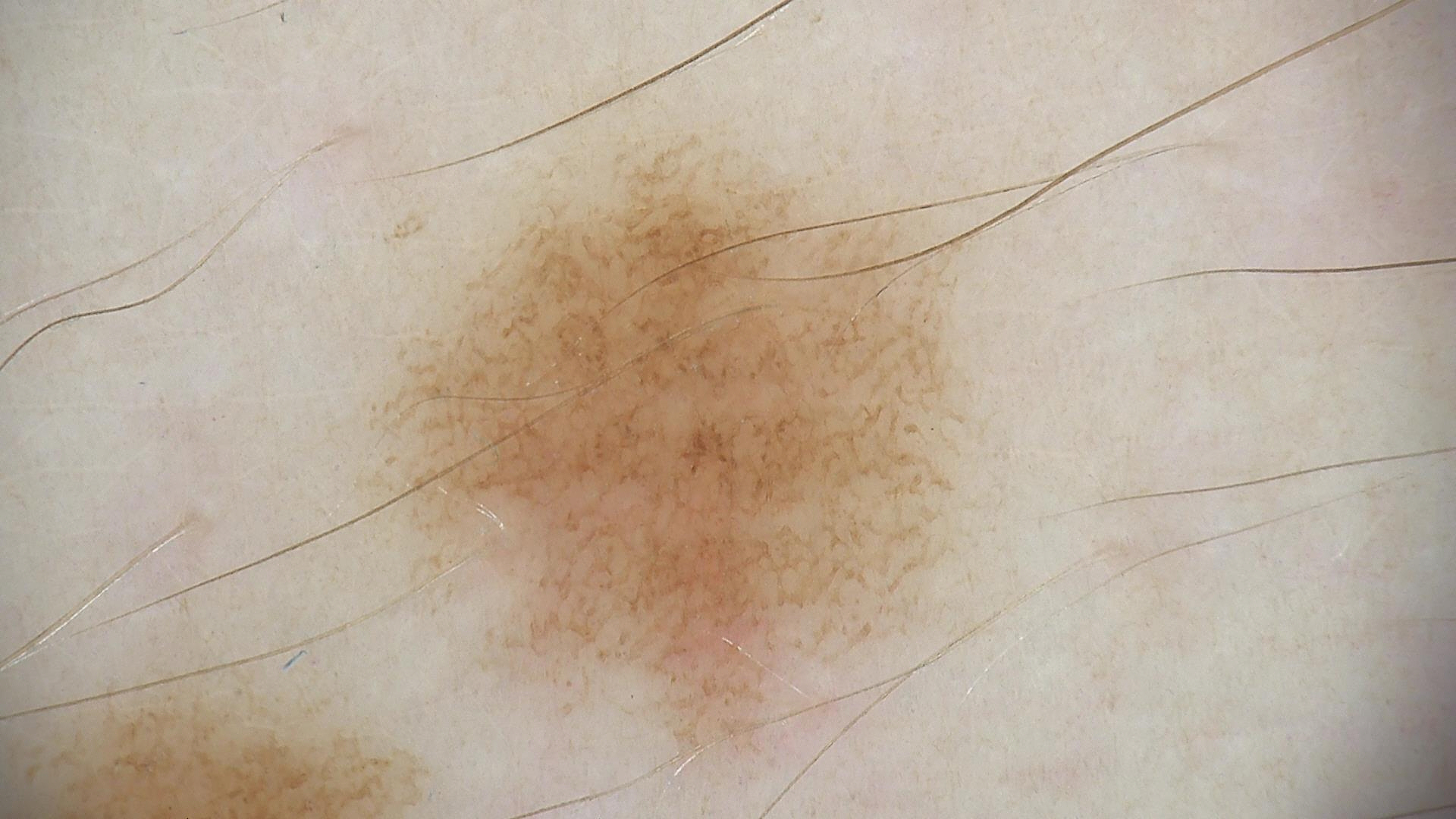Q: What is the imaging modality?
A: dermatoscopy
Q: What was the diagnostic impression?
A: dysplastic junctional nevus (expert consensus)